The back of the hand is involved; the photo was captured at an angle; the contributor is a female aged 40–49.
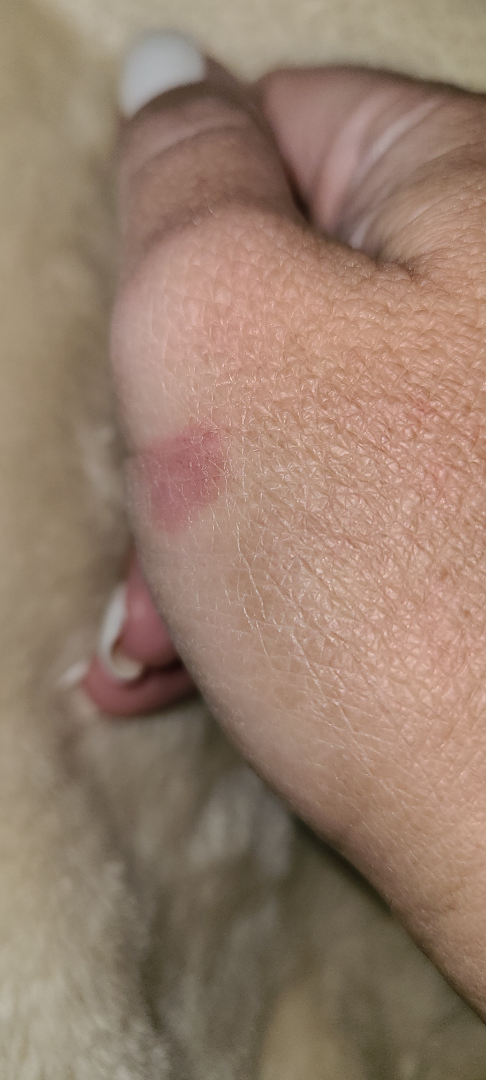Findings:
Contact dermatitis (primary); Eczema (remote); Burn erythema of back of hand (remote); Acute dermatitis, NOS (remote); Phytophotodermatitis (remote); Irritant Contact Dermatitis (remote).